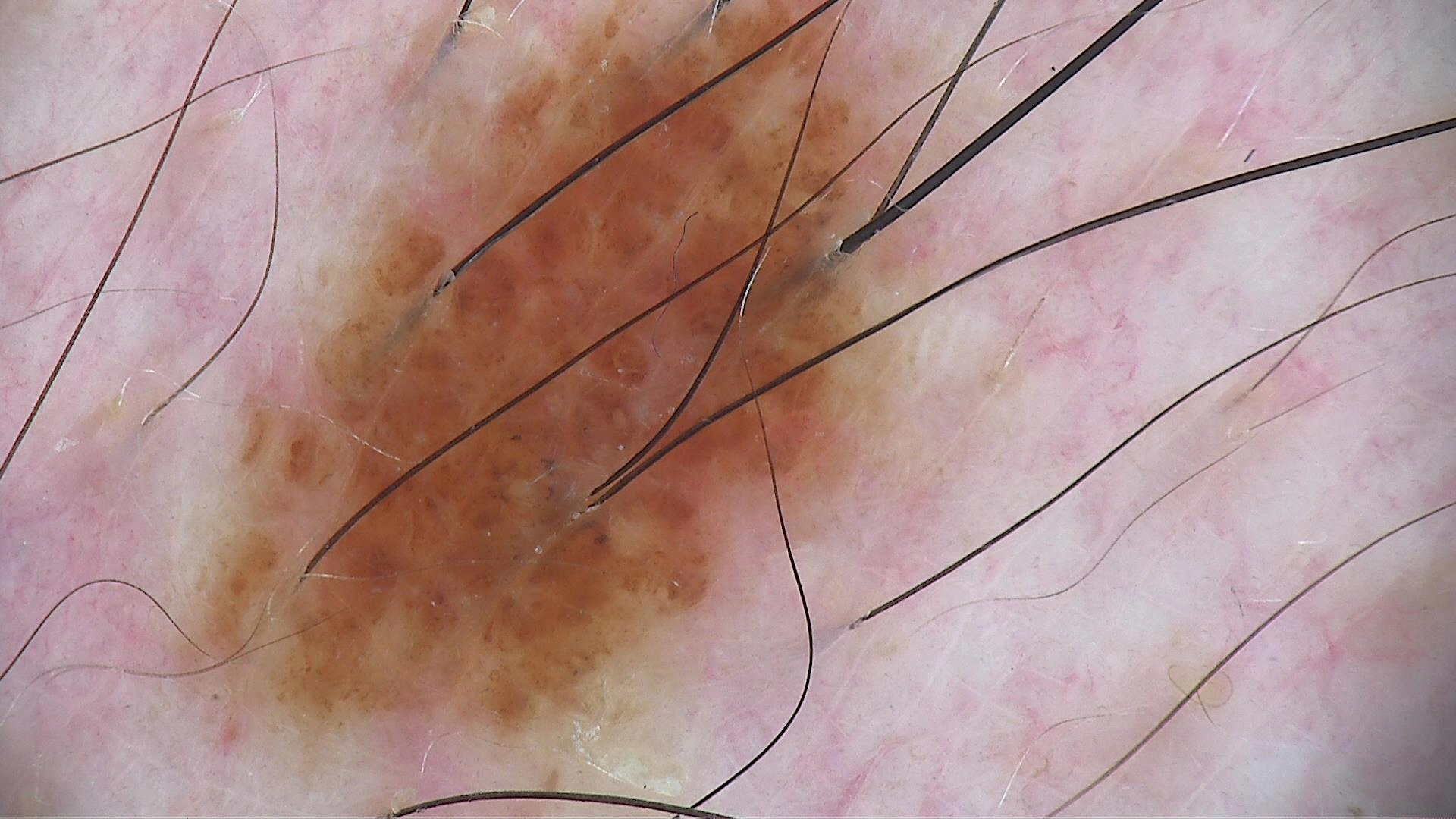Conclusion: Classified as a dysplastic compound nevus.